Close-up view · the lesion involves the head or neck, front of the torso, leg, back of the hand and arm — 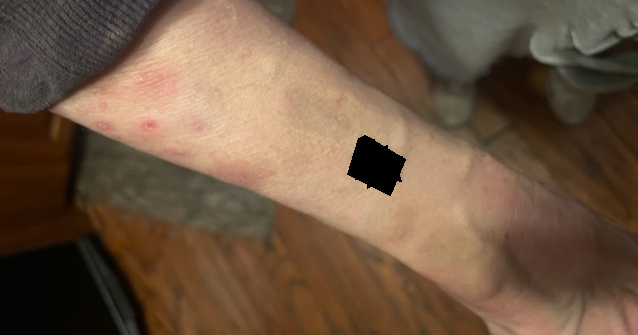Q: What was the assessment?
A: not assessable
Q: Any systemic symptoms?
A: none reported
Q: What symptoms does the patient report?
A: bothersome appearance, itching and enlargement
Q: What is the lesion texture?
A: flat and raised or bumpy
Q: Patient's own categorization?
A: skin that appeared healthy to them
Q: How long has this been present?
A: one to four weeks